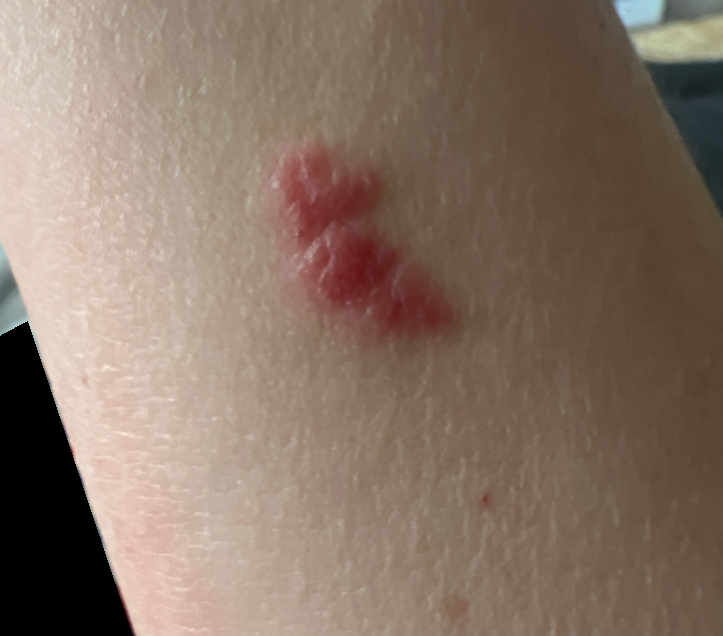Q: What was the assessment?
A: ungradable on photographic review
Q: What is the affected area?
A: arm
Q: What is the framing?
A: close-up